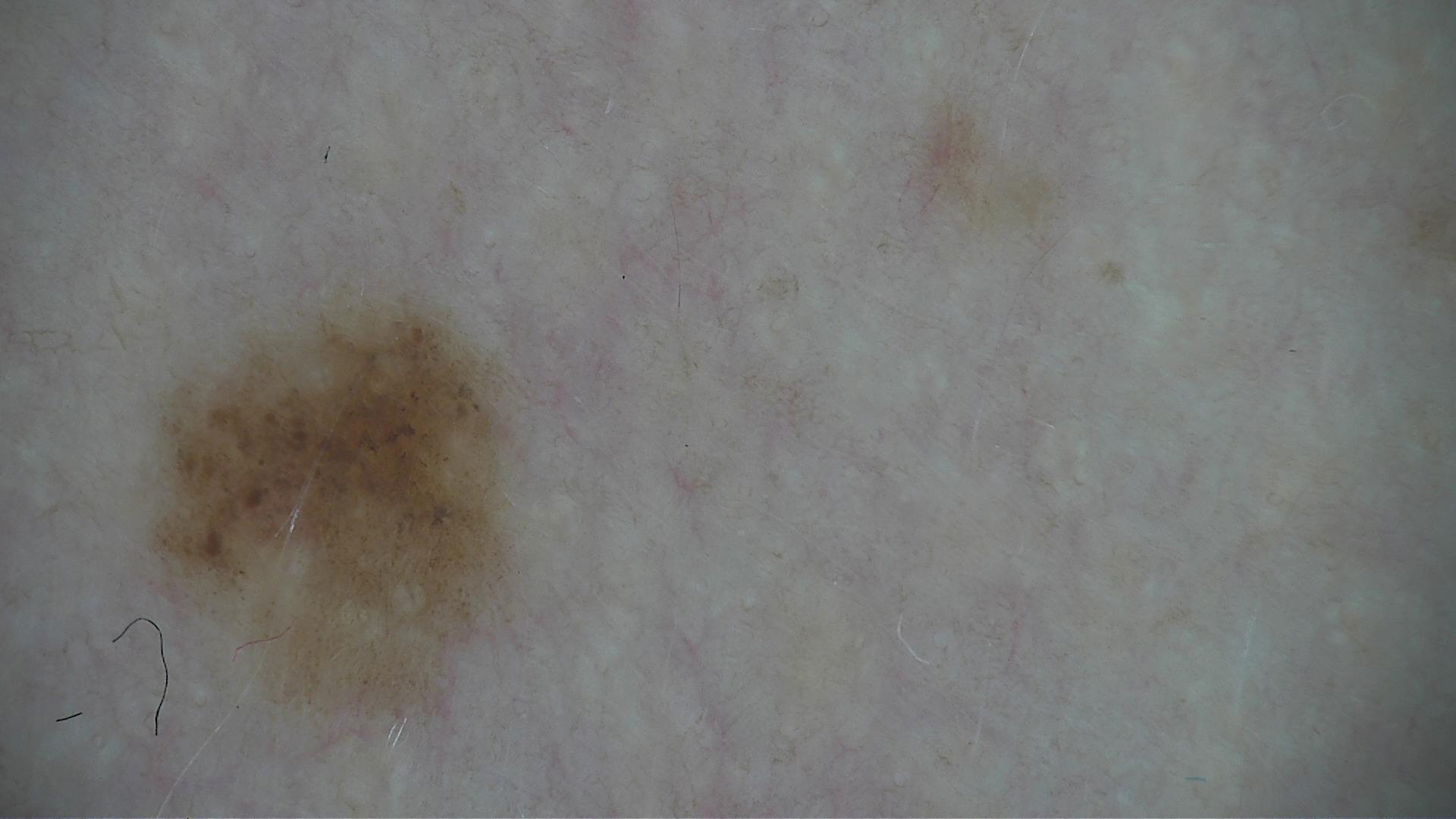Classified as a dysplastic junctional nevus.